The lesion involves the leg; close-up view: 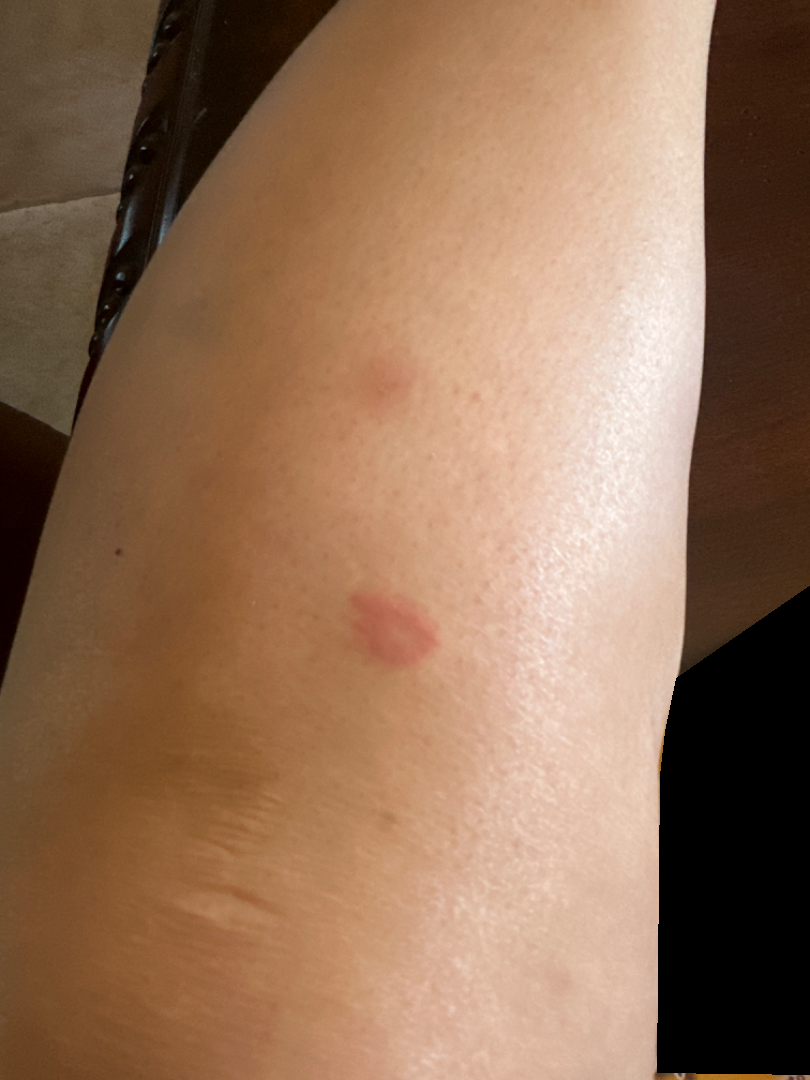History:
The patient reports the lesion is raised or bumpy and fluid-filled.
Impression:
On photographic review: Allergic Contact Dermatitis (most likely); Eczema (possible).